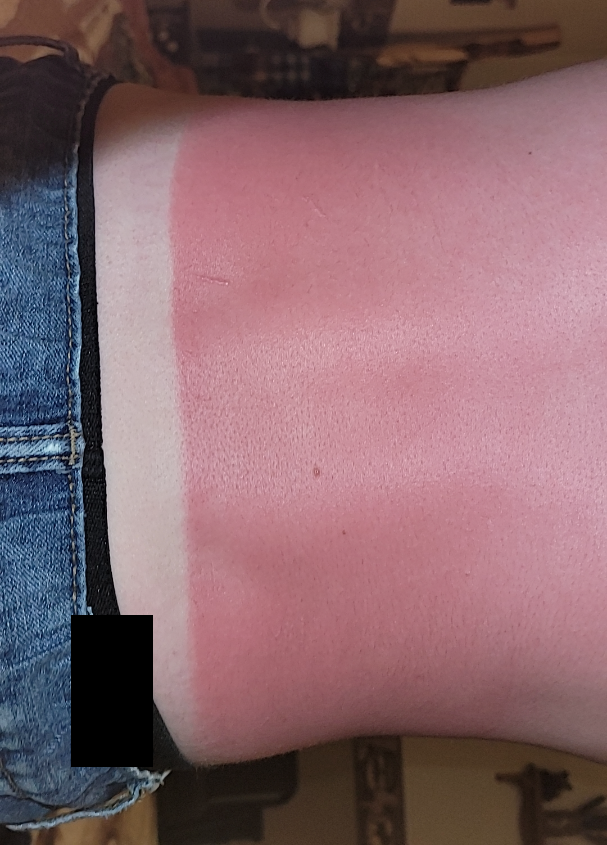Close-up view.
On photographic review by a dermatologist, Photodermatitis (favored).